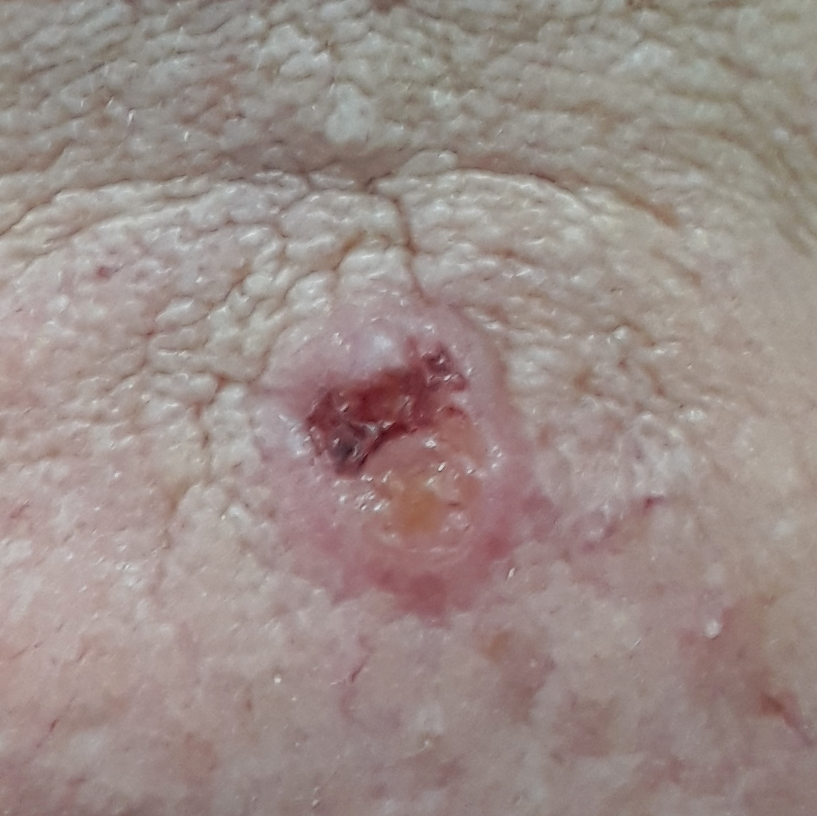diagnosis = basal cell carcinoma (biopsy-proven).